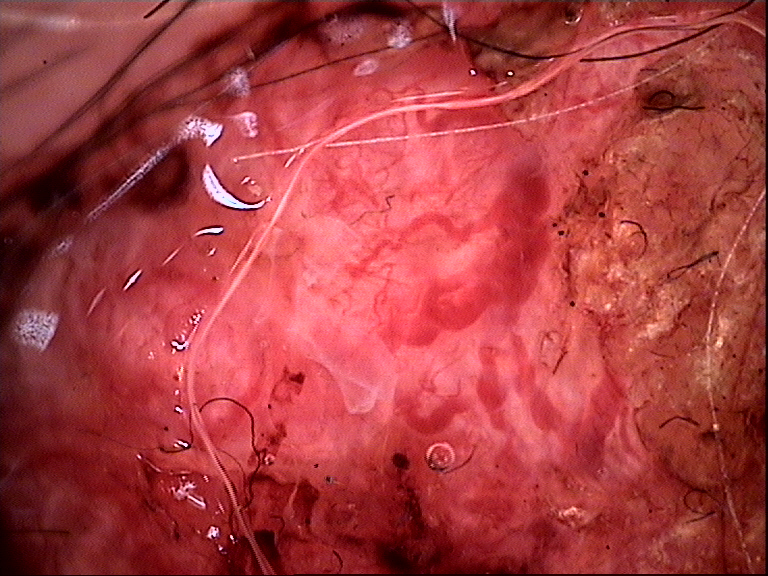Biopsy-confirmed as a basal cell carcinoma.